No constitutional symptoms were reported; an image taken at a distance; reported duration is one to four weeks; the patient considered this a rash; reported lesion symptoms include itching; the lesion is described as flat; the affected area is the back of the torso; male subject, age 18–29: 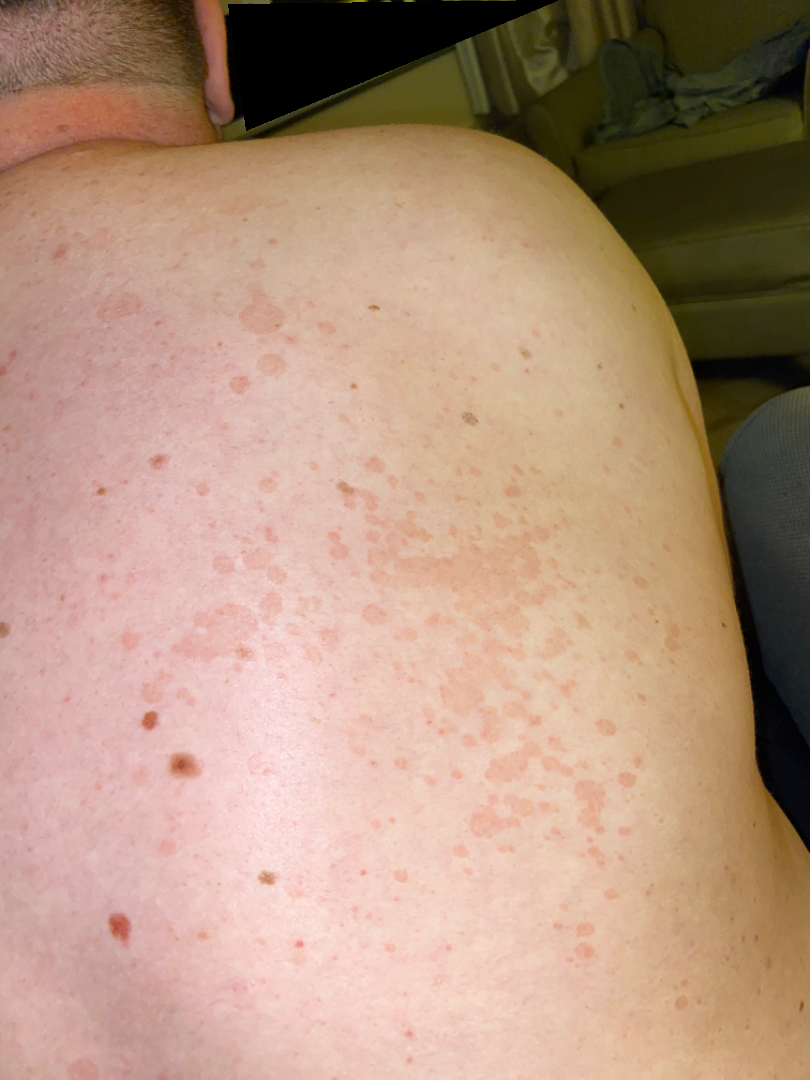impression — favoring Tinea Versicolor; lower on the differential is Pityriasis rosea; less probable is Seborrheic Dermatitis; less likely is Tinea; a more distant consideration is Eczema